The chart records prior malignancy (patient or family) and alcohol use · the patient is Fitzpatrick phototype II · a male subject in their 40s · a clinical photograph showing a skin lesion: 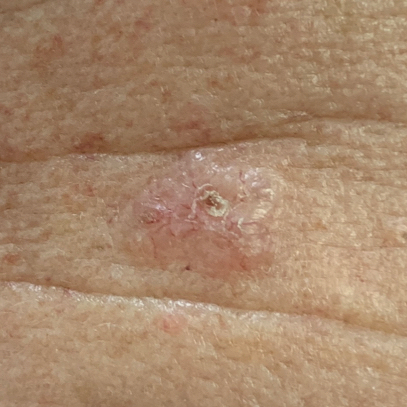diameter = 10 × 6 mm; reported symptoms = elevation, itching; diagnosis = basal cell carcinoma (biopsy-proven).